A dermatoscopic image of a skin lesion.
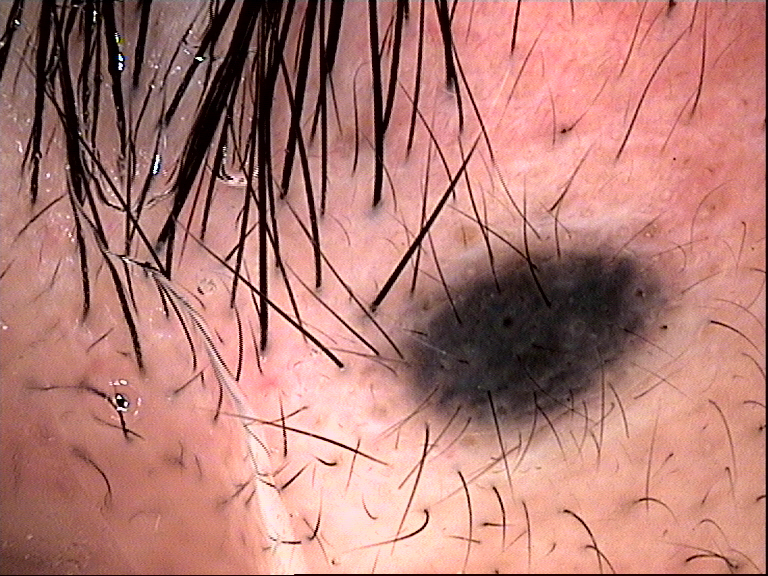assessment=blue nevus (expert consensus).